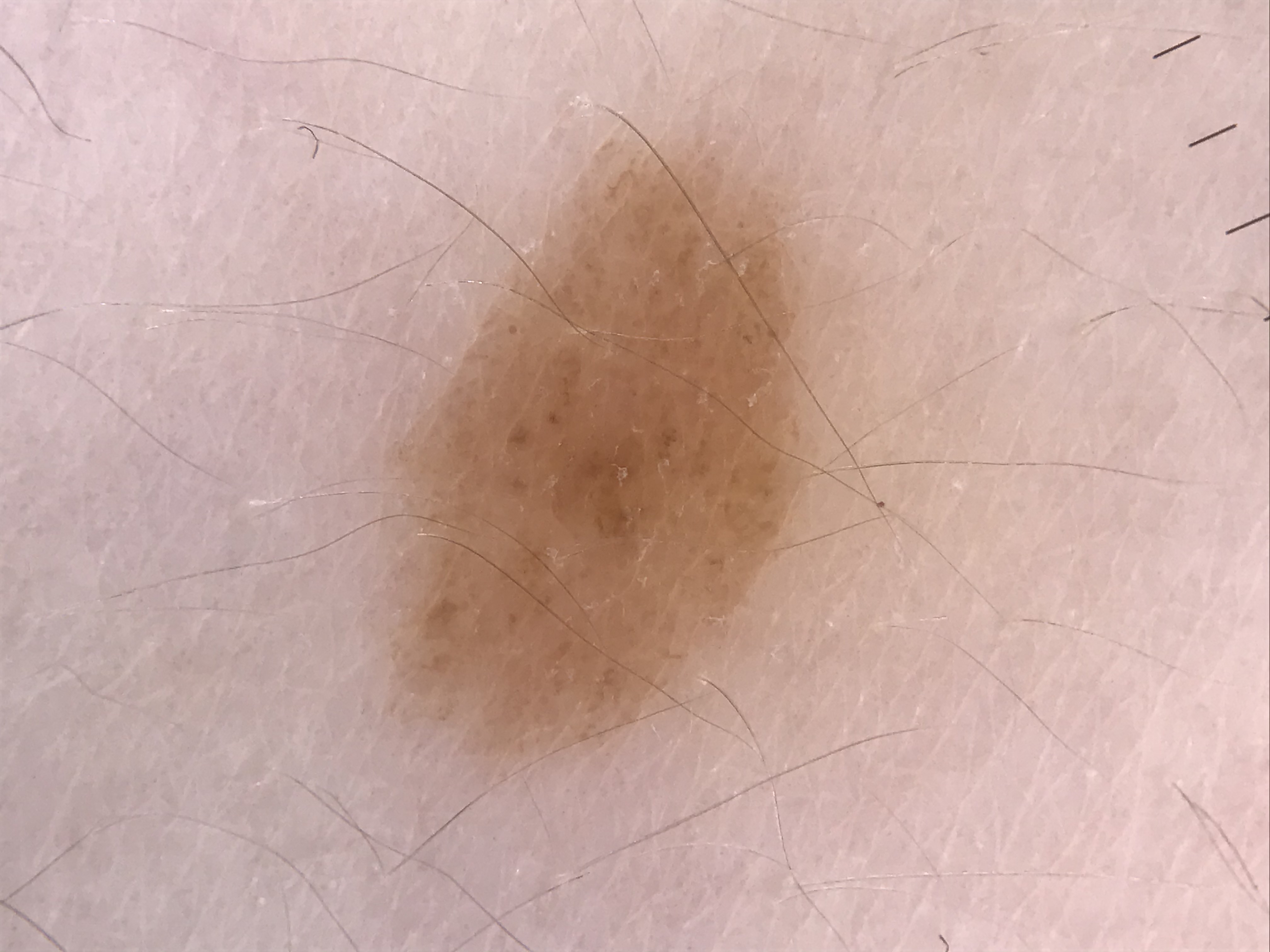Impression:
Diagnosed as a benign lesion — a dysplastic compound nevus.